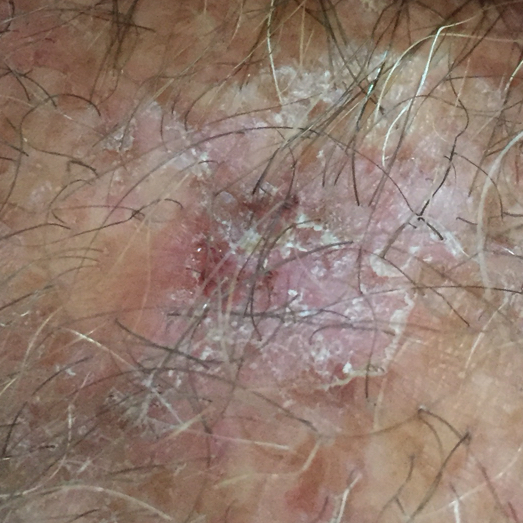A patient 54 years of age.
A clinical photograph showing a skin lesion.
The lesion is located on a forearm.
Per patient report, the lesion has bled, itches, and hurts, but has not grown and has not changed.
Expert review favored an actinic keratosis.